The photograph was taken at an angle; the subject is a male aged 60–69; located on the arm; self-categorized by the patient as skin that appeared healthy to them; the lesion is associated with itching; skin tone: self-reported Fitzpatrick phototype IV; no constitutional symptoms were reported: 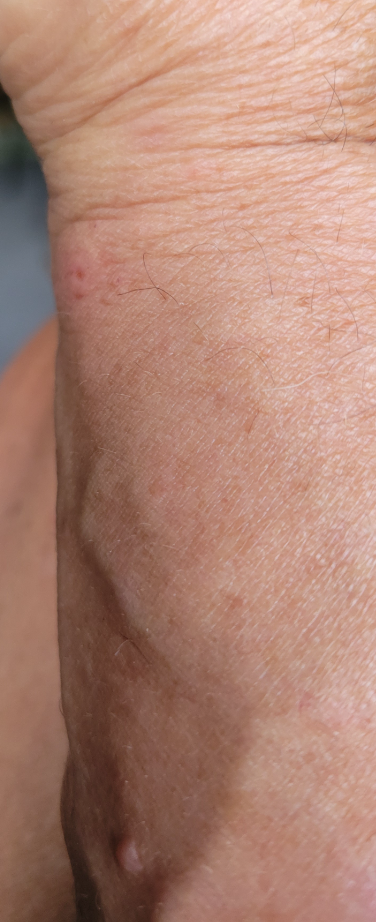| field | value |
|---|---|
| assessment | could not be assessed |